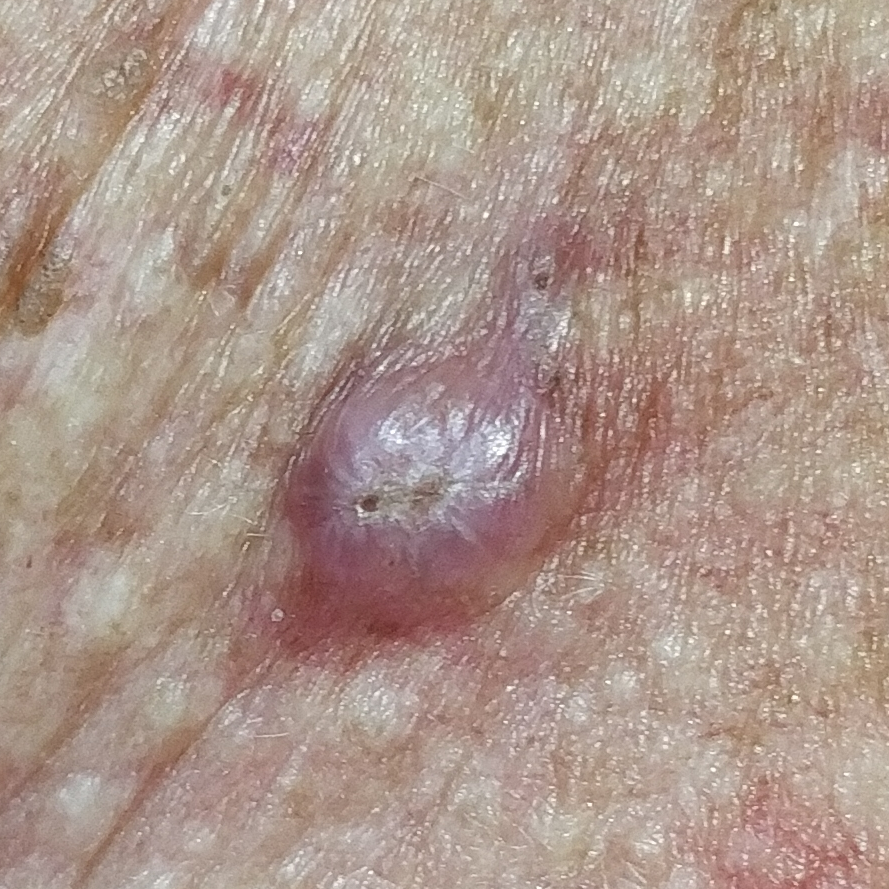Recorded as Fitzpatrick III.
The lesion is located on the neck.
The lesion measures approximately 6 × 5 mm.
The biopsy diagnosis was a squamous cell carcinoma.